A dermatoscopic image of a skin lesion: 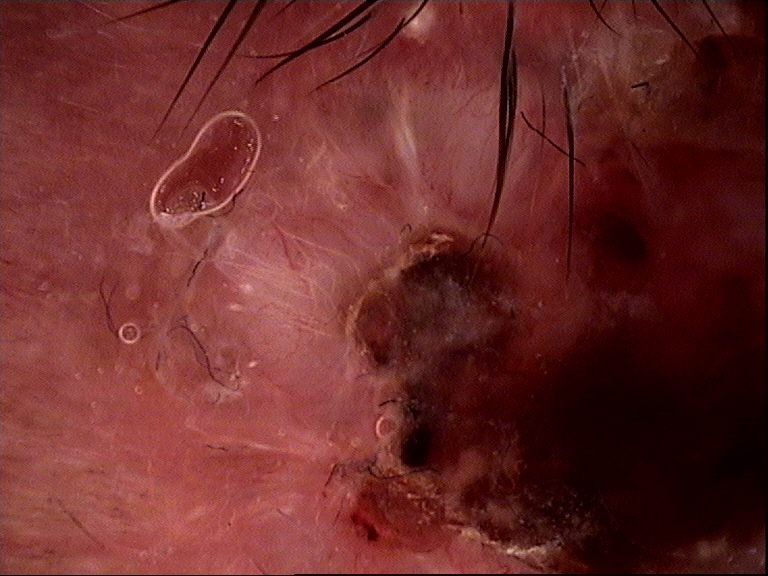category = keratinocytic; diagnostic label = basal cell carcinoma (biopsy-proven).